A clinical photograph of a skin lesion.
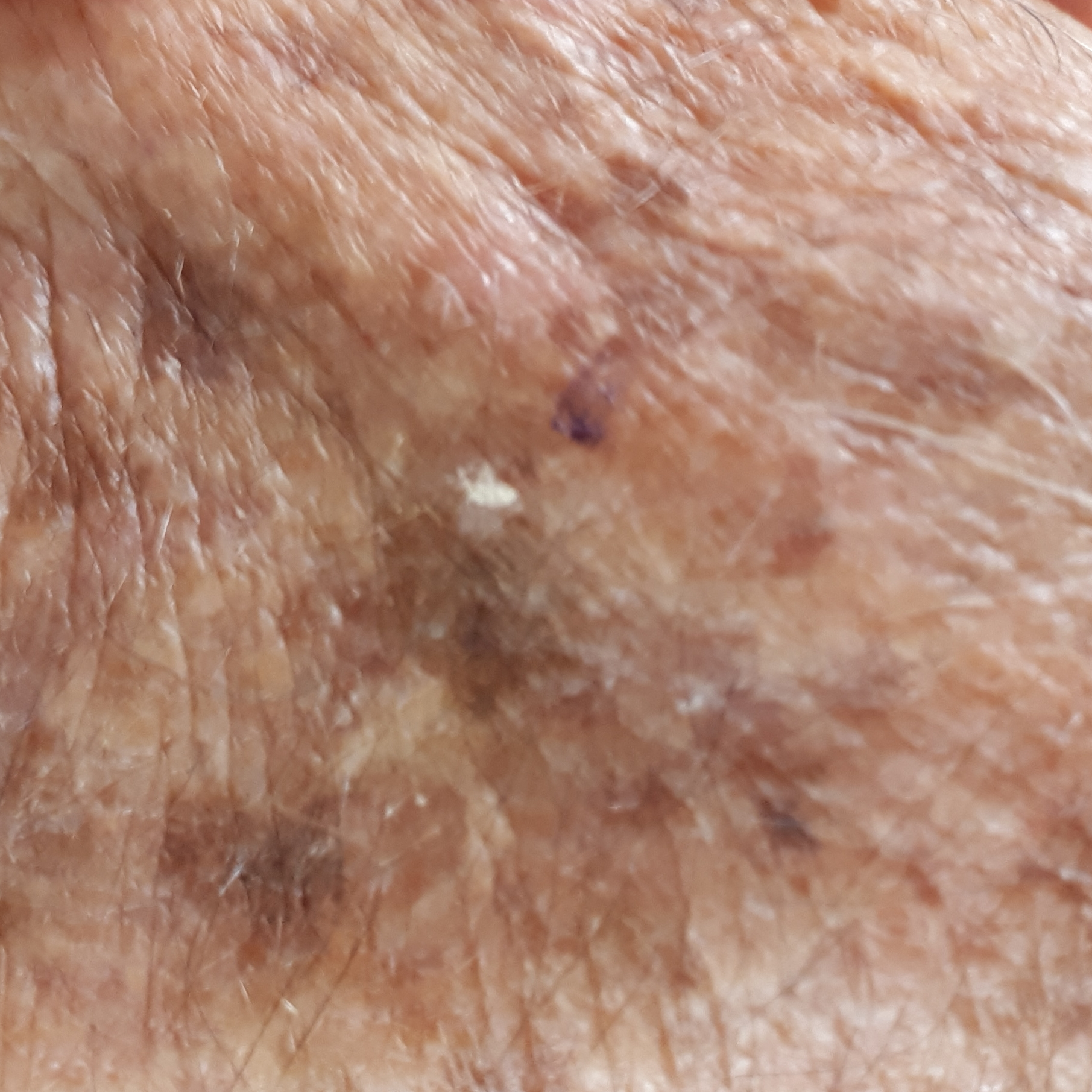Q: What is the anatomic site?
A: a hand
Q: What symptoms does the patient report?
A: itching
Q: What is the diagnosis?
A: actinic keratosis (clinical consensus)